The photograph was taken at a distance. Male contributor, age 18–29.
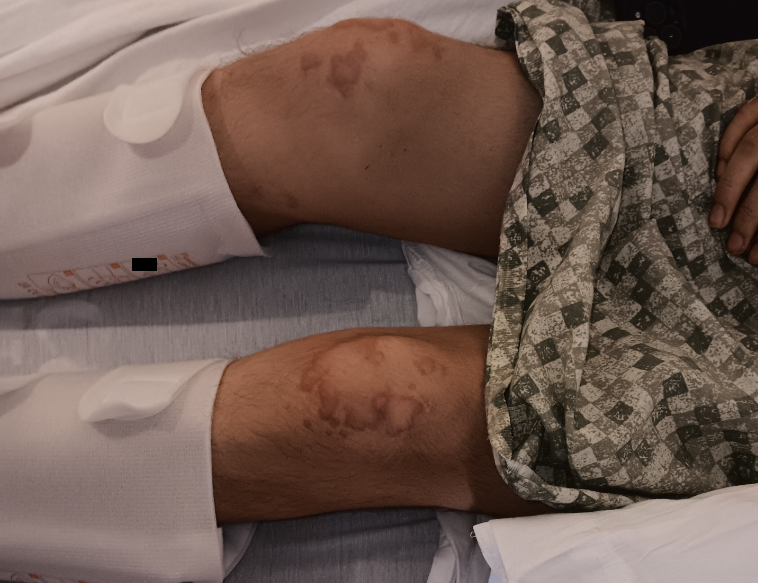Review:
The reviewing panel's impression was: favoring Rheumatoid nodule; also consider gouty tophi; possibly Granuloma annulare.